Fitzpatrick II · the photograph is a close-up of the affected area · the patient is a female aged 18–29 — 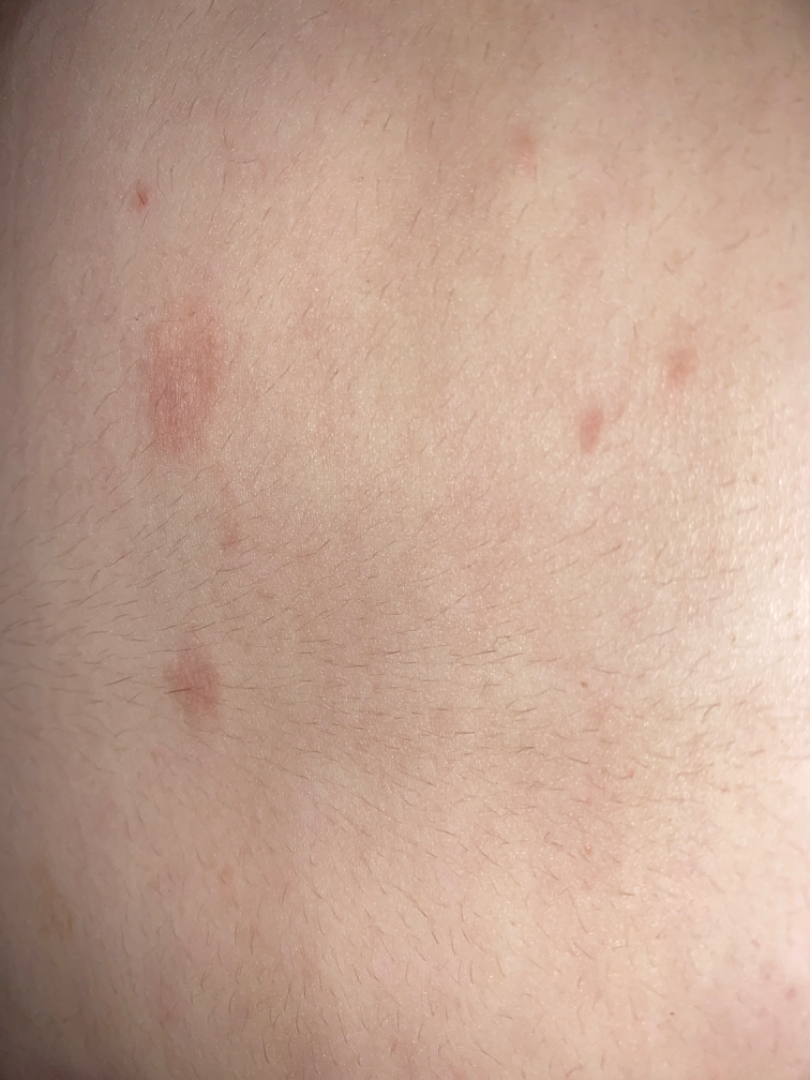assessment=indeterminate from the photograph.